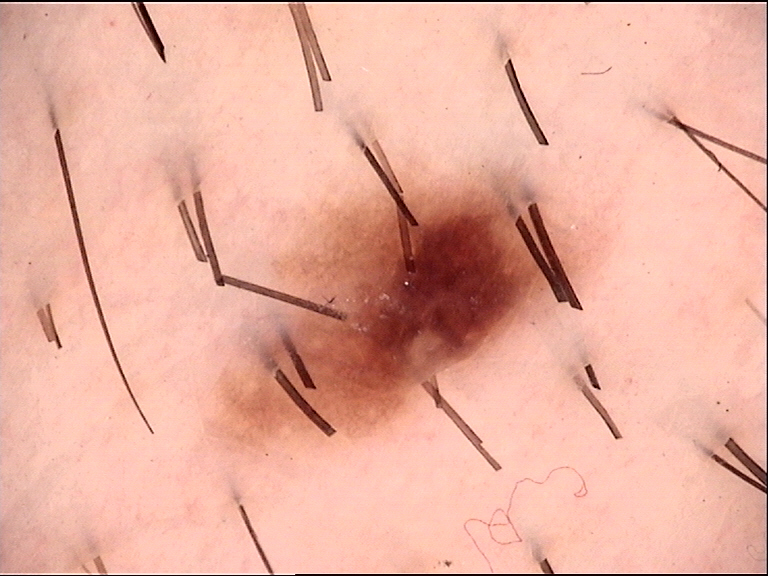diagnosis:
  name: dysplastic compound nevus
  code: cd
  malignancy: benign
  super_class: melanocytic
  confirmation: expert consensus